A dermoscopic image of a skin lesion.
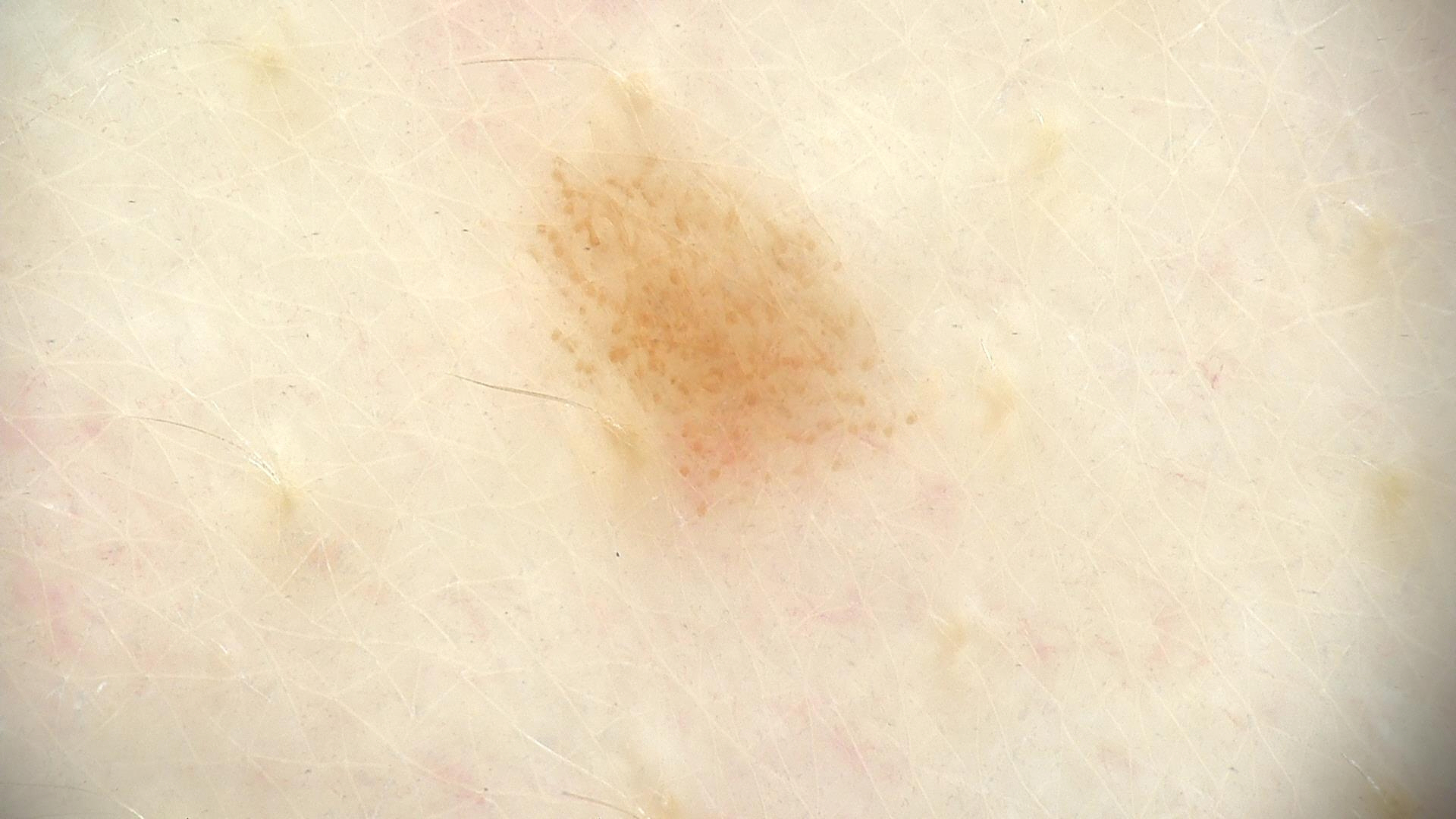The diagnosis was a dysplastic junctional nevus.